Dermoscopy of a skin lesion:
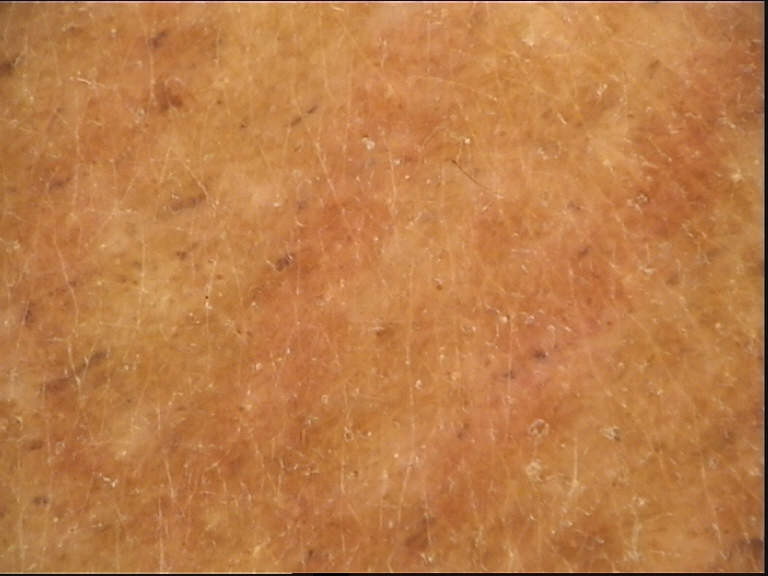Case:
- diagnosis · congenital junctional nevus (expert consensus)